The photograph is a close-up of the affected area; located on the head or neck — 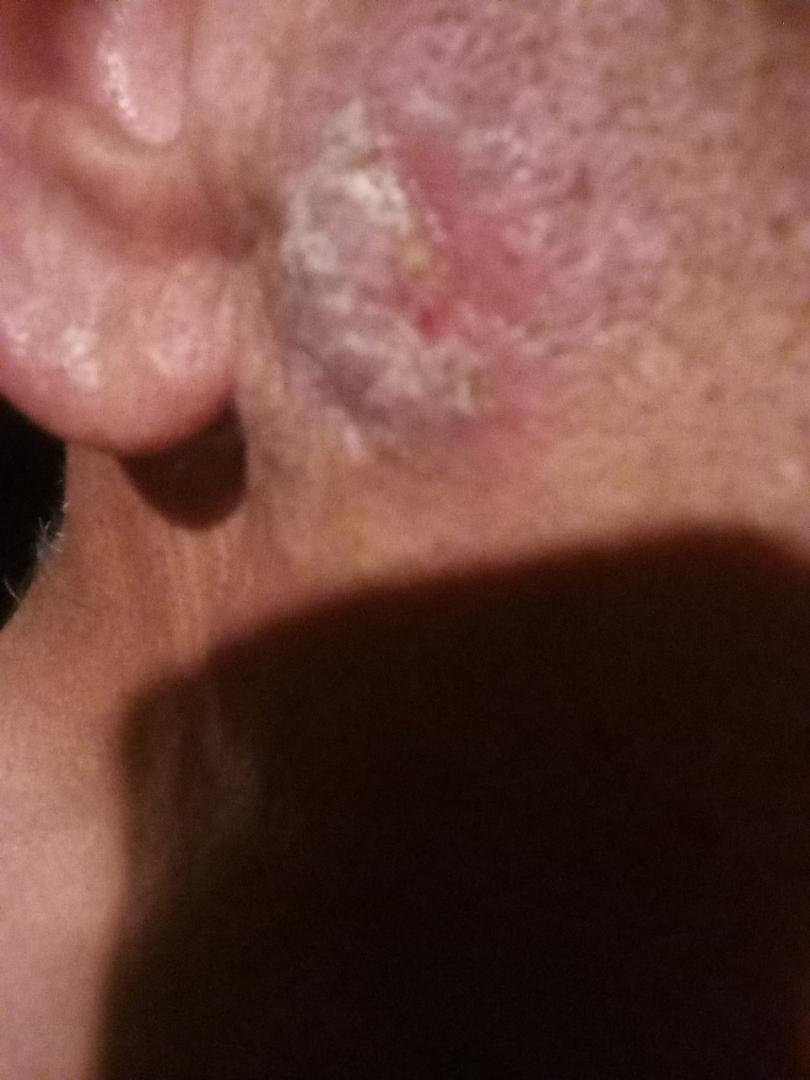Impression:
The condition could not be reliably identified from the image.
History:
Associated systemic symptoms include joint pain and fatigue. Human graders estimated Monk skin tone scale 4 or 5.